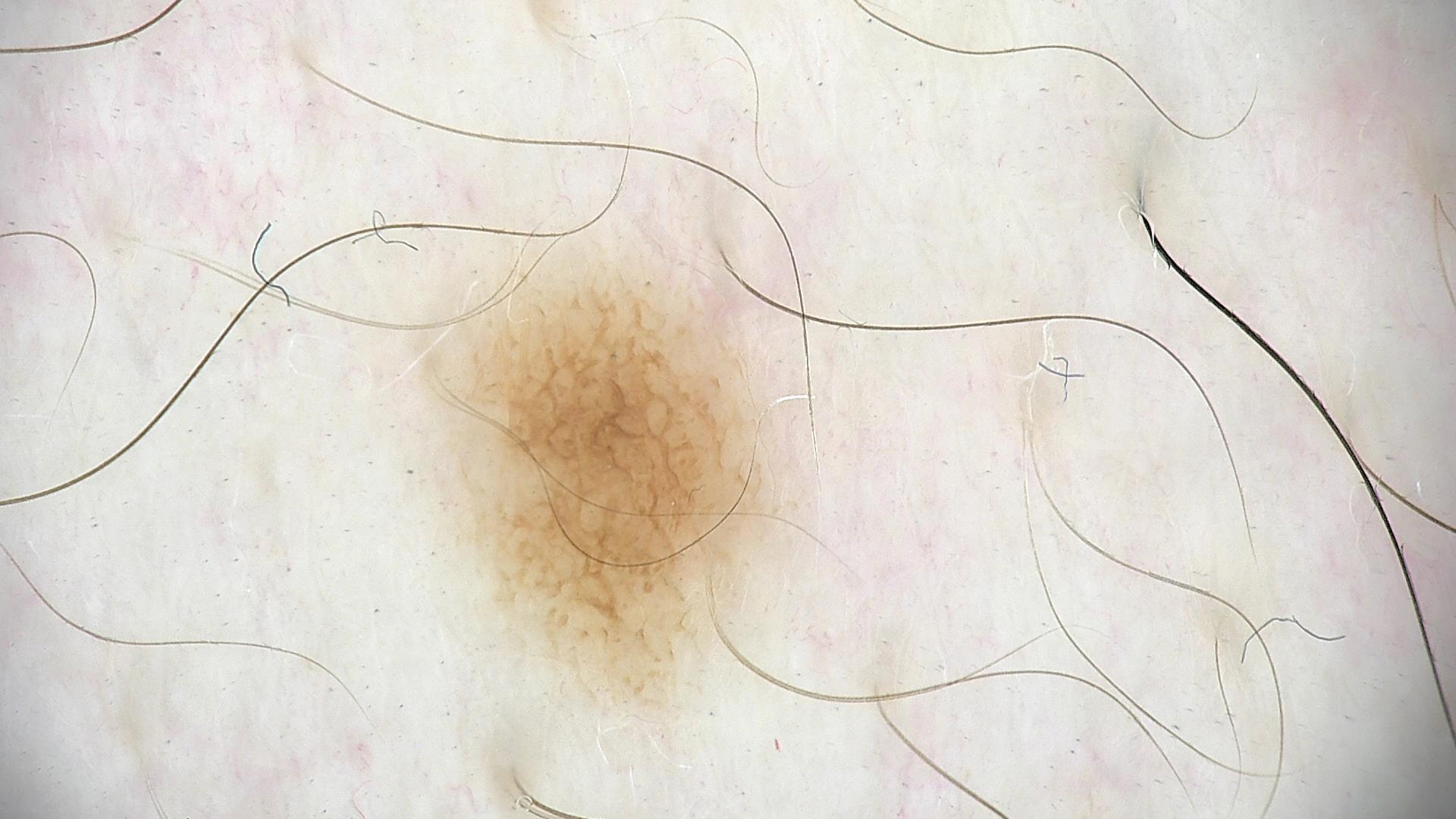Diagnosed as a junctional nevus.